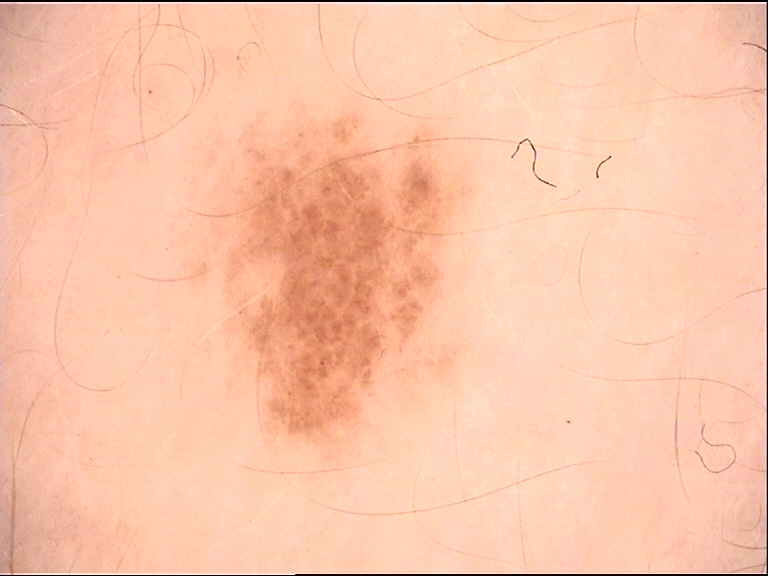Summary: Dermoscopy of a skin lesion. Impression: The diagnosis was a banal lesion — a junctional nevus.